The photograph was taken at an angle. Reported lesion symptoms include burning and itching. The arm and leg are involved. The patient considered this a rash. The condition has been present for one to four weeks — 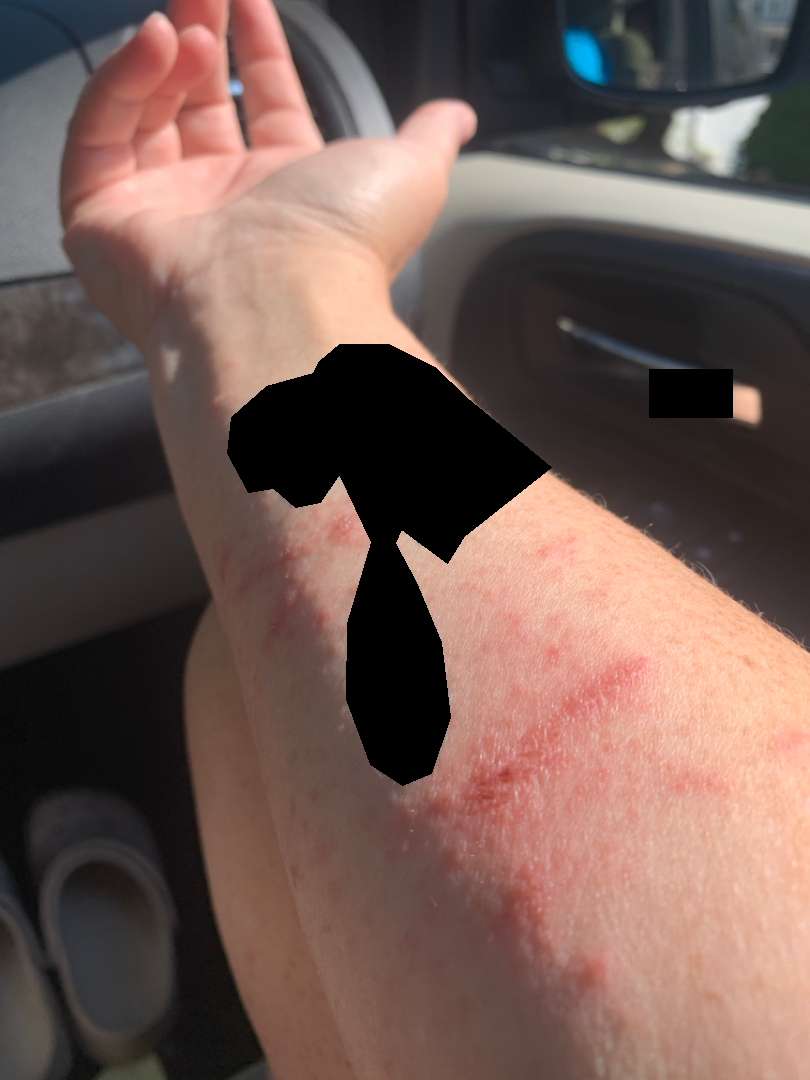Most consistent with Allergic Contact Dermatitis.